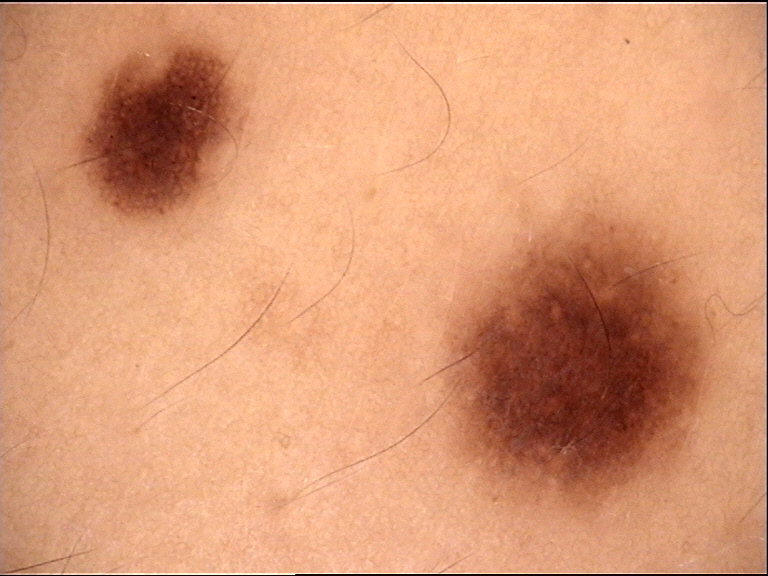Q: What is this lesion?
A: junctional nevus (expert consensus)